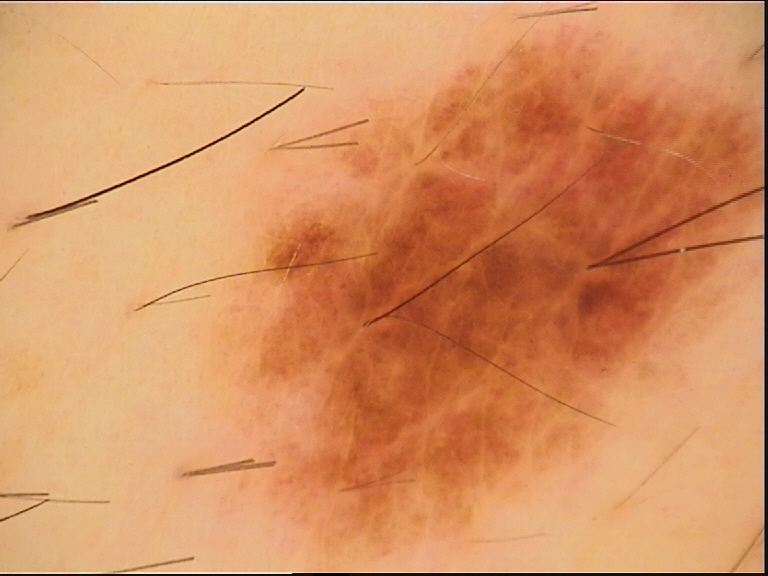image type: dermatoscopy
diagnostic label: dysplastic compound nevus (expert consensus)